A dermatoscopic image of a skin lesion.
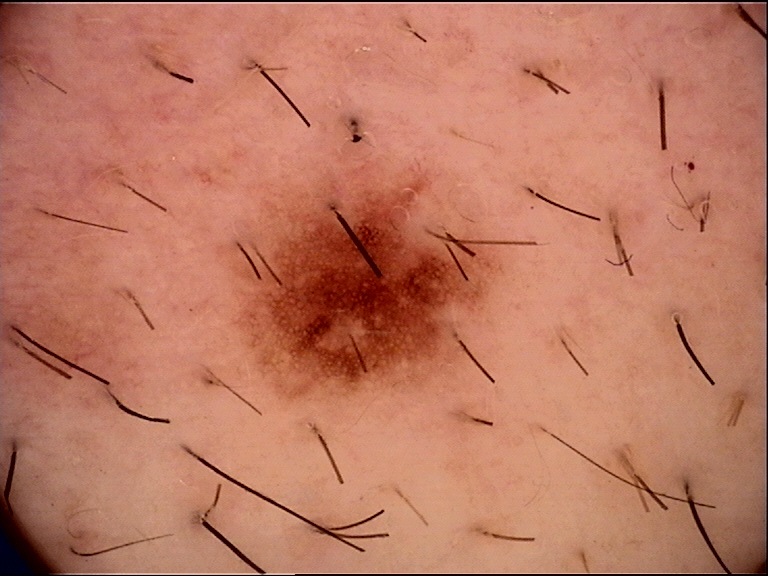diagnosis: dysplastic junctional nevus (expert consensus).